The arm is involved · this is a close-up image.
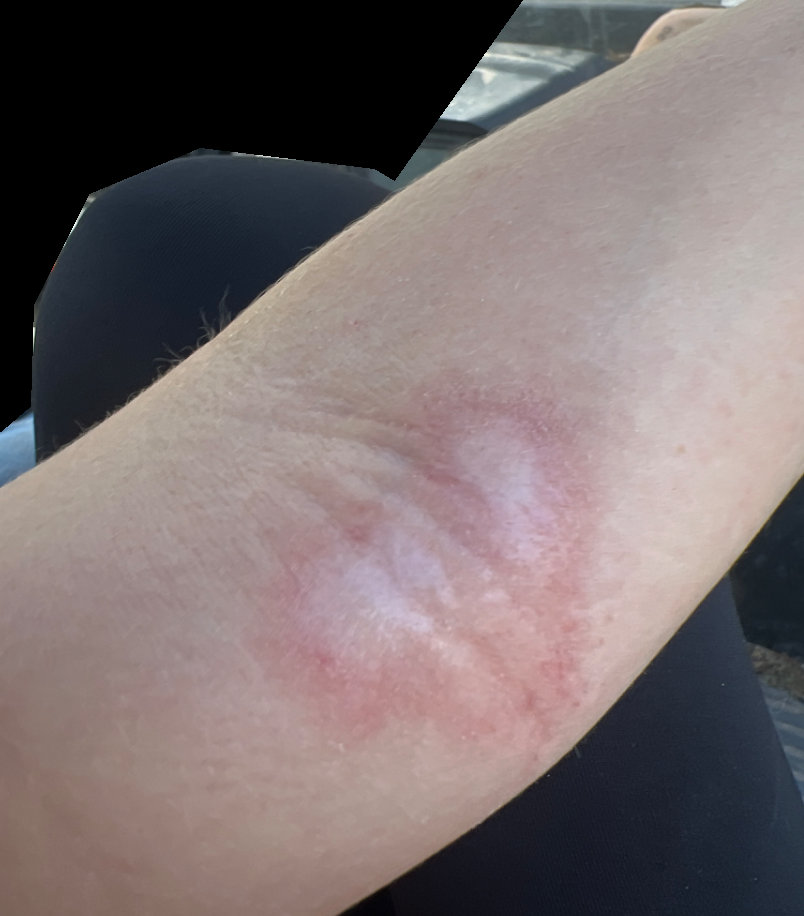<summary>
<skin_tone>
  <fitzpatrick>III</fitzpatrick>
</skin_tone>
<texture>rough or flaky</texture>
<systemic_symptoms>fatigue</systemic_symptoms>
<symptoms>enlargement, itching, bothersome appearance, burning</symptoms>
<patient_category>a rash</patient_category>
<duration>one to four weeks</duration>
<differential>
  <leading>Morphea/Scleroderma</leading>
  <considered>Eczema</considered>
</differential>
</summary>